Collected as part of a research study, without a referral diagnosis · a male patient 77 years of age · dermoscopy of a skin lesion:
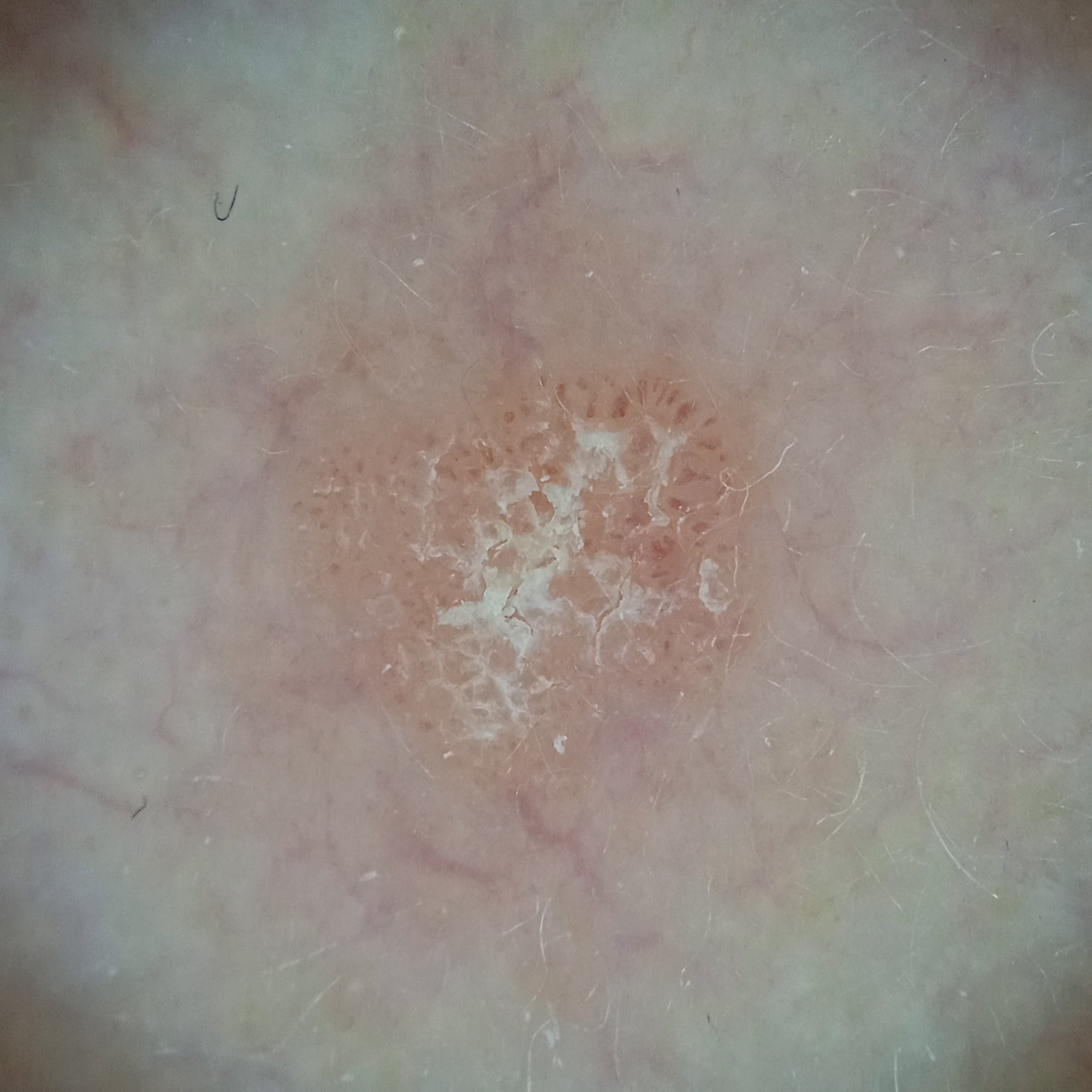diagnosis: actinic keratosis (dermatologist consensus).